Recorded as Fitzpatrick II · a wide-field clinical photograph of a skin lesion · a patient roughly 55 years of age:
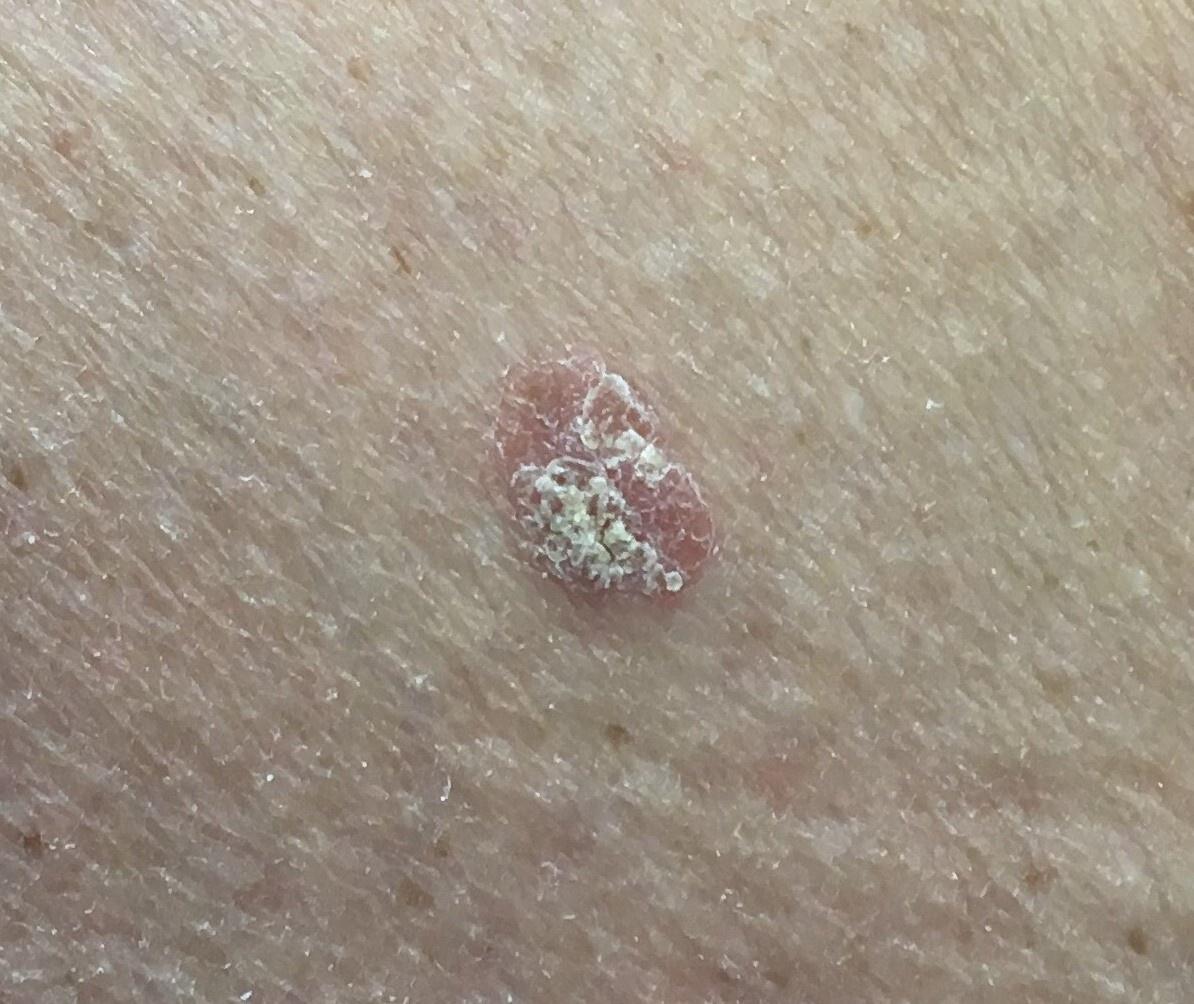The lesion involves a lower extremity. Biopsy-confirmed as a squamous cell carcinoma.